A dermoscopic photograph of a skin lesion.
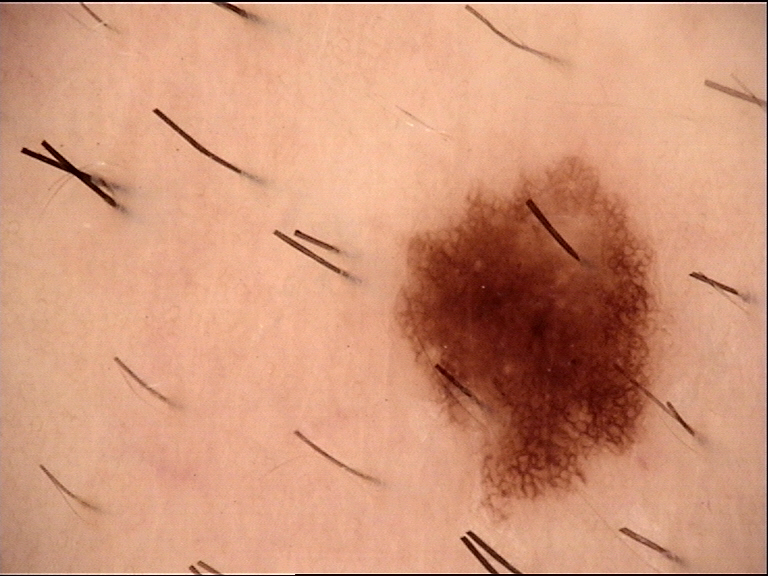Labeled as a dysplastic junctional nevus.